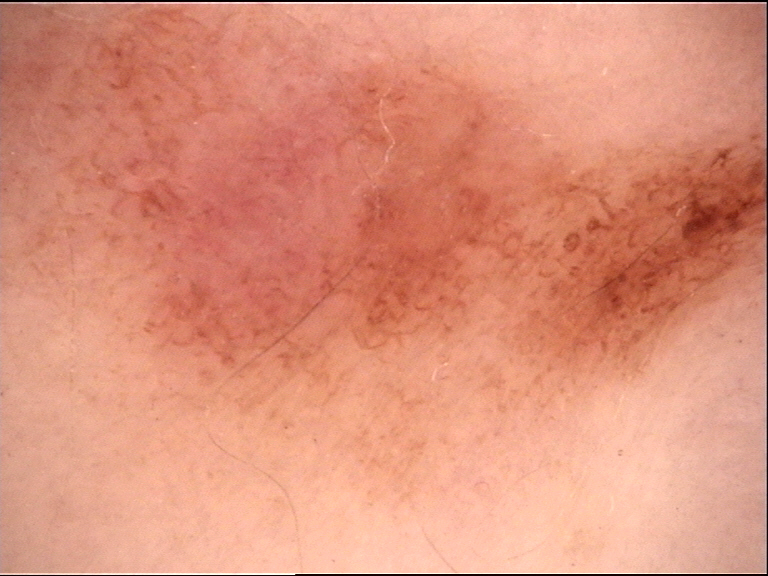image type: dermoscopy
diagnostic label: dysplastic junctional nevus (expert consensus)